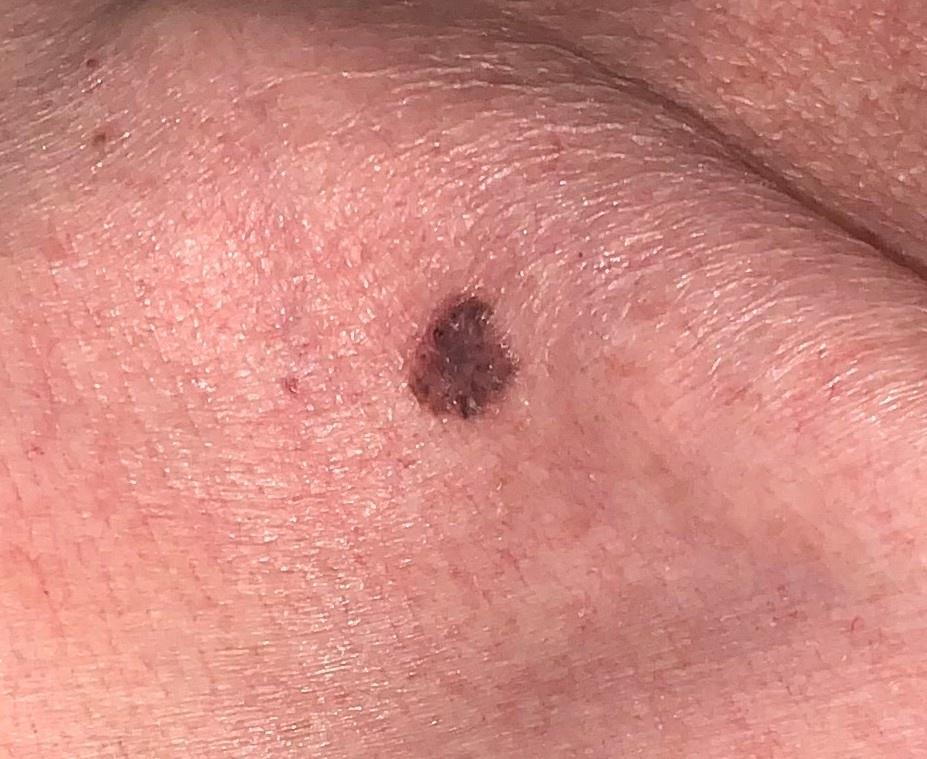| key | value |
|---|---|
| subject | female, about 55 years old |
| modality | clinical photograph |
| location | the trunk (the anterior trunk) |
| diagnostic label | Basal cell carcinoma (biopsy-proven) |